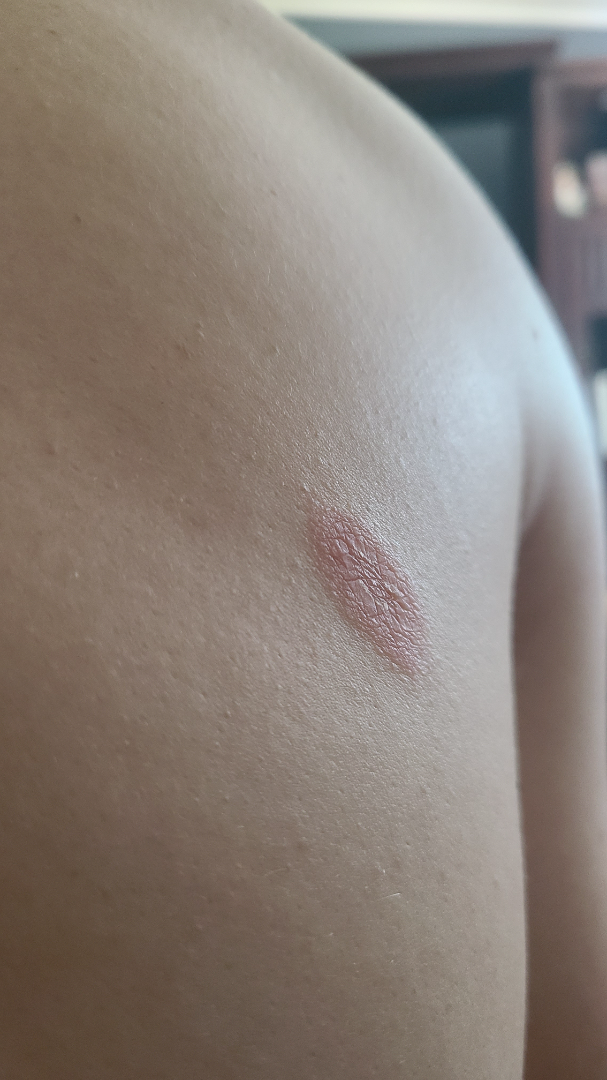Q: Reported symptoms?
A: bothersome appearance
Q: What is the patient's skin tone?
A: lay reviewers estimated Monk skin tone scale 1–2
Q: What is the lesion texture?
A: rough or flaky
Q: Where on the body?
A: back of the torso
Q: Duration?
A: one to four weeks
Q: Patient's own categorization?
A: skin that appeared healthy to them
Q: Image view?
A: at an angle
Q: What is the dermatologist's impression?
A: favoring Pityriasis rosea